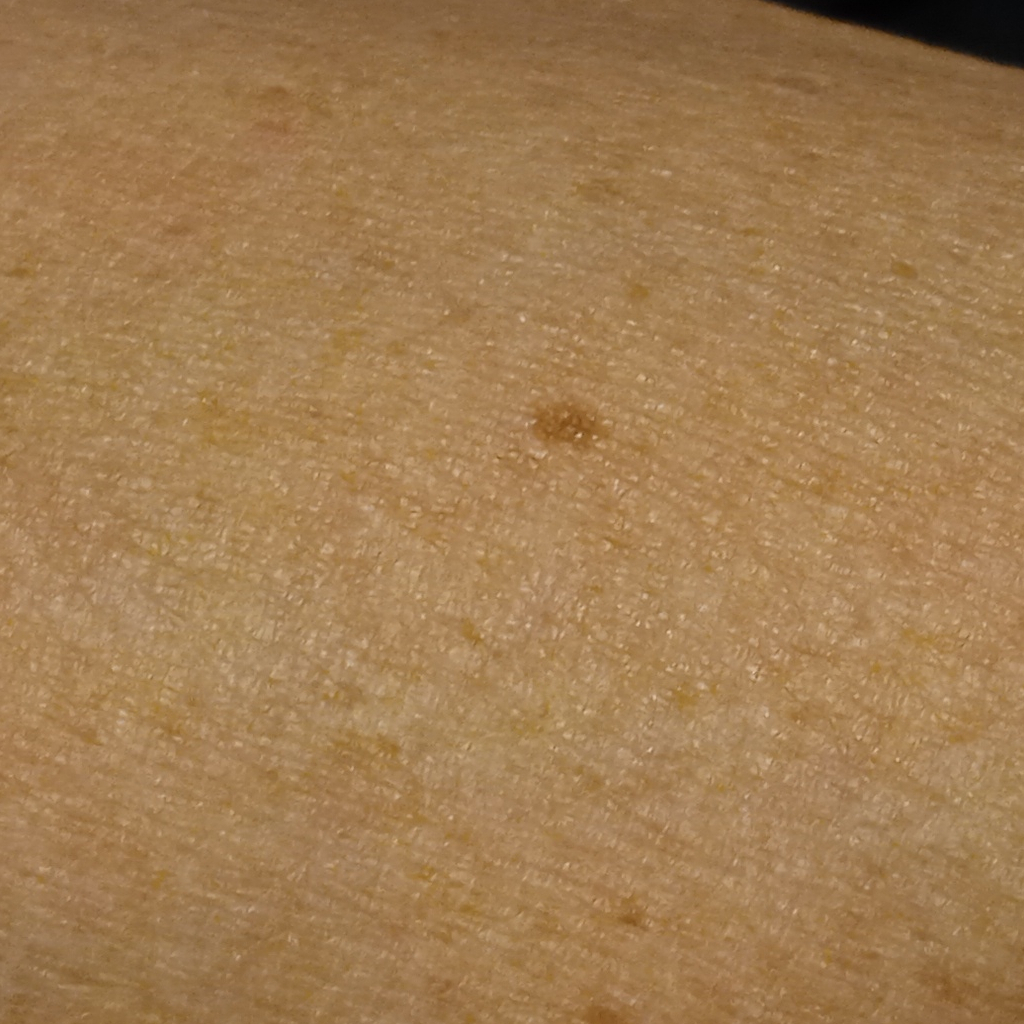A female patient aged 67. A macroscopic clinical photograph of a skin lesion. The patient says their skin reddens with sun exposure. On a questionnaire the patient reported a personal history of skin cancer. Located on an arm. The lesion is about 2.3 mm across. Dermatologist review favored a melanocytic nevus.